A male subject approximately 40 years of age · recorded as FST III: 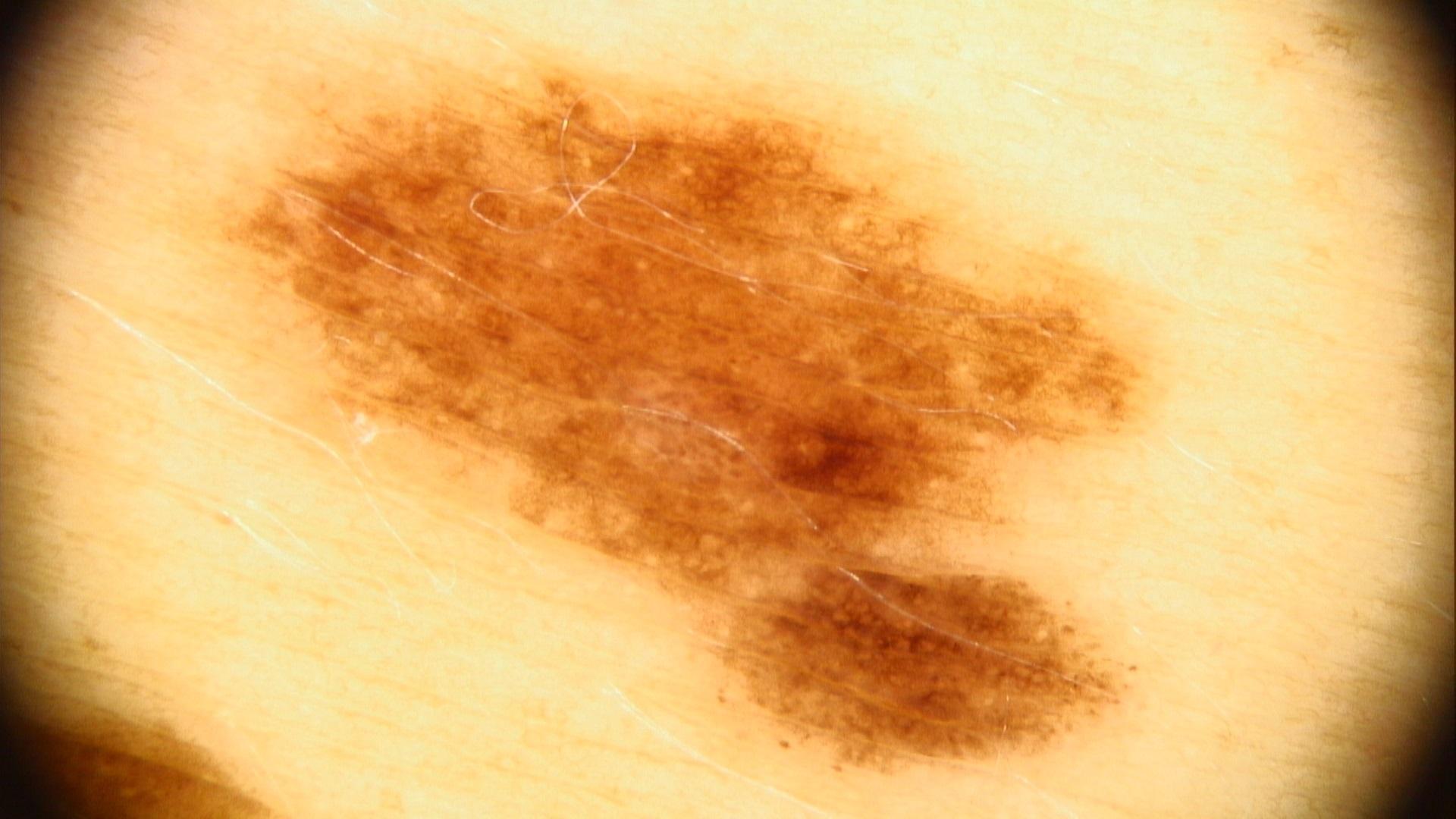<case>
<lesion_location>
<region>the trunk</region>
<detail>the posterior trunk</detail>
</lesion_location>
<diagnosis>
<name>Nevus</name>
<malignancy>benign</malignancy>
<confirmation>expert clinical impression</confirmation>
<lineage>melanocytic</lineage>
</diagnosis>
</case>